A dermoscopy image of a single skin lesion.
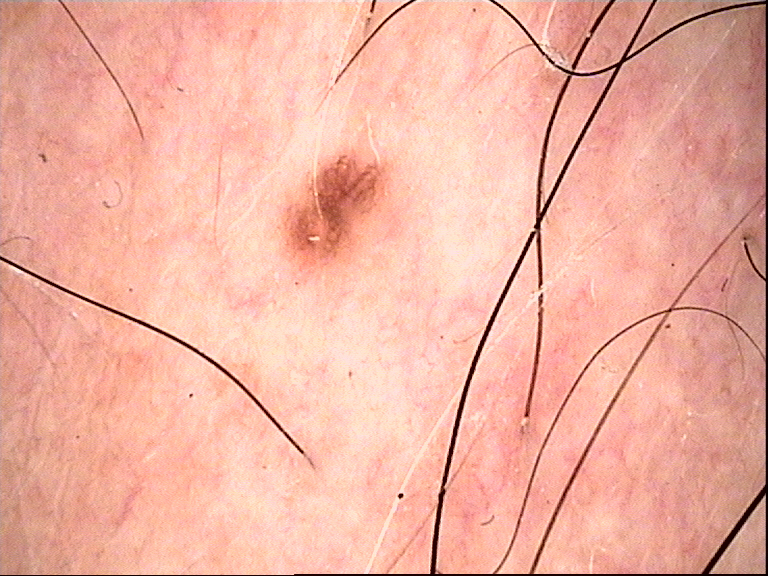Impression: Consistent with a junctional nevus.